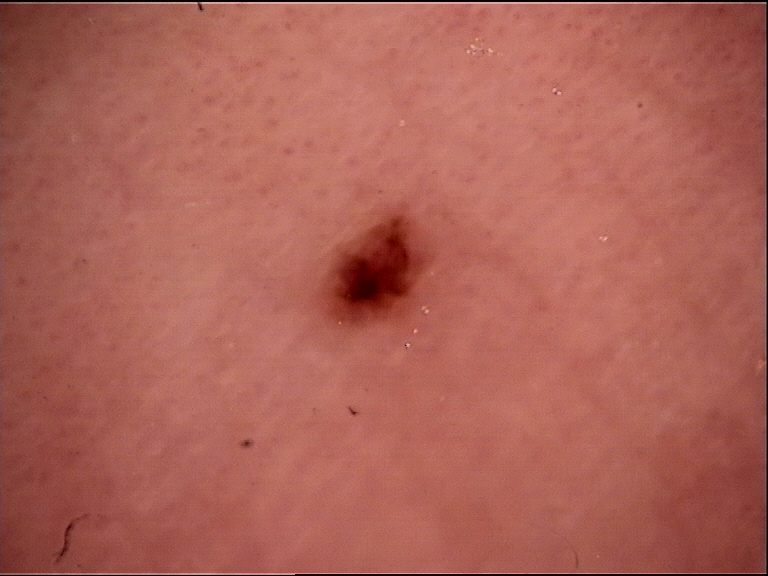The diagnostic label was a dysplastic junctional nevus.